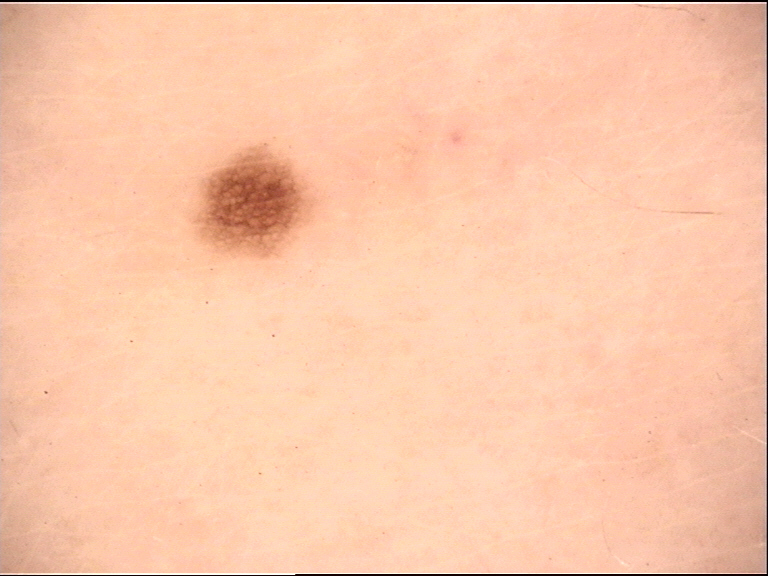The diagnosis was a dysplastic junctional nevus.